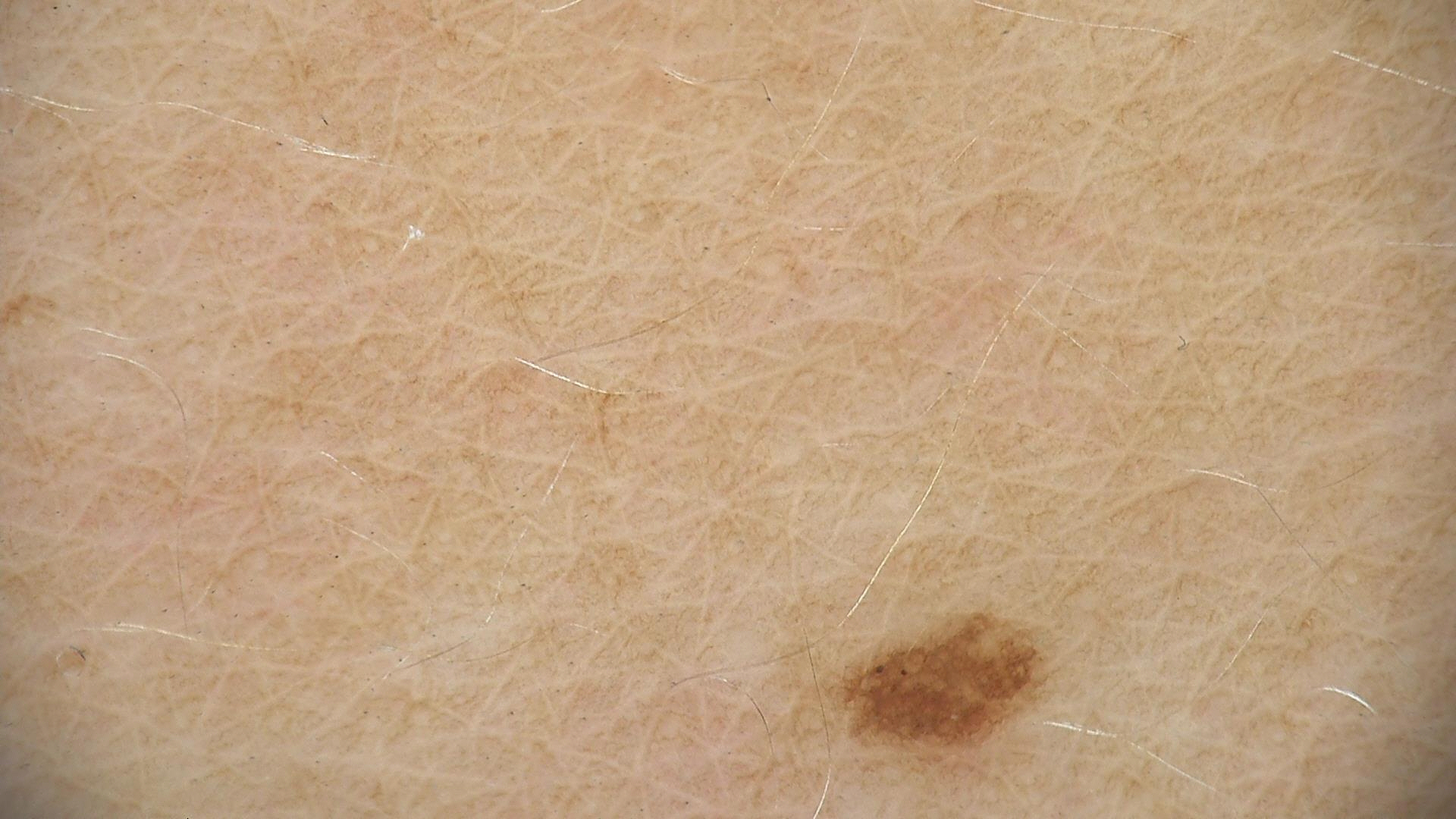Findings:
A dermoscopy image of a single skin lesion.
Impression:
Consistent with a dysplastic junctional nevus.